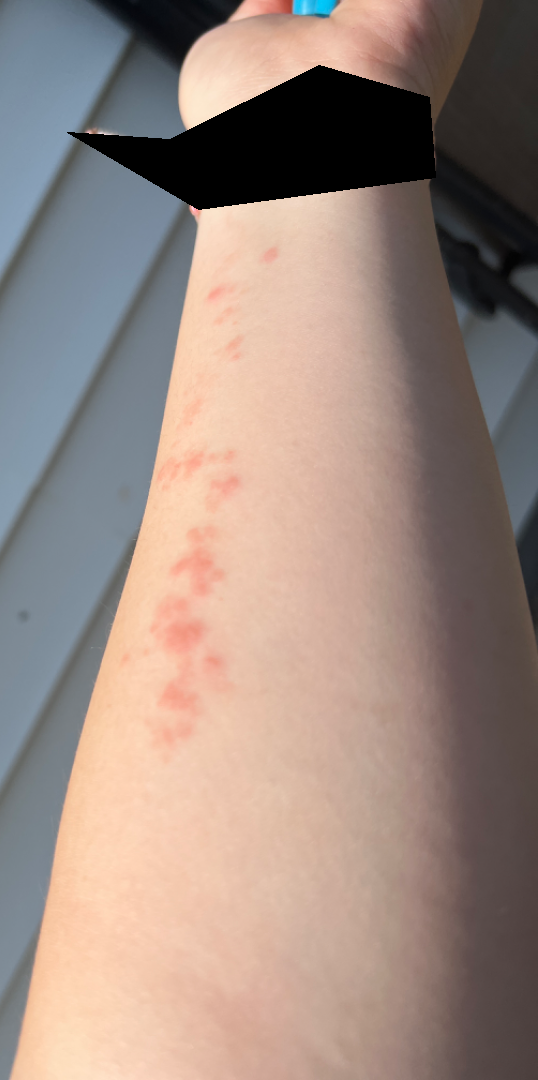Patient information: Reported duration is one to three months. No constitutional symptoms were reported. Female contributor, age 18–29. The photograph was taken at an angle. Symptoms reported: enlargement, bleeding, bothersome appearance and itching. Texture is reported as raised or bumpy. Located on the arm. Self-categorized by the patient as a rash. Review: On photographic review by a dermatologist, Insect Bite and Allergic Contact Dermatitis were each considered, in no particular order; less probable is Herpes Zoster.